The photograph was taken at an angle. The contributor is female: 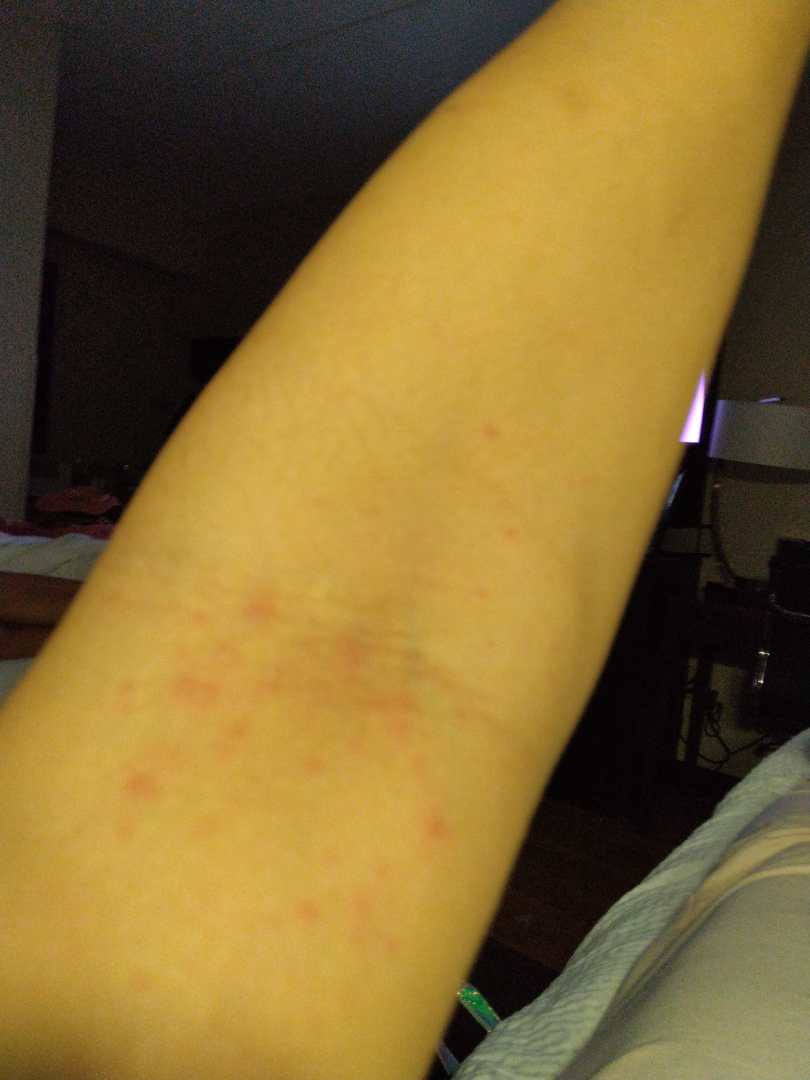The image was not sufficient for the reviewer to characterize the skin condition.